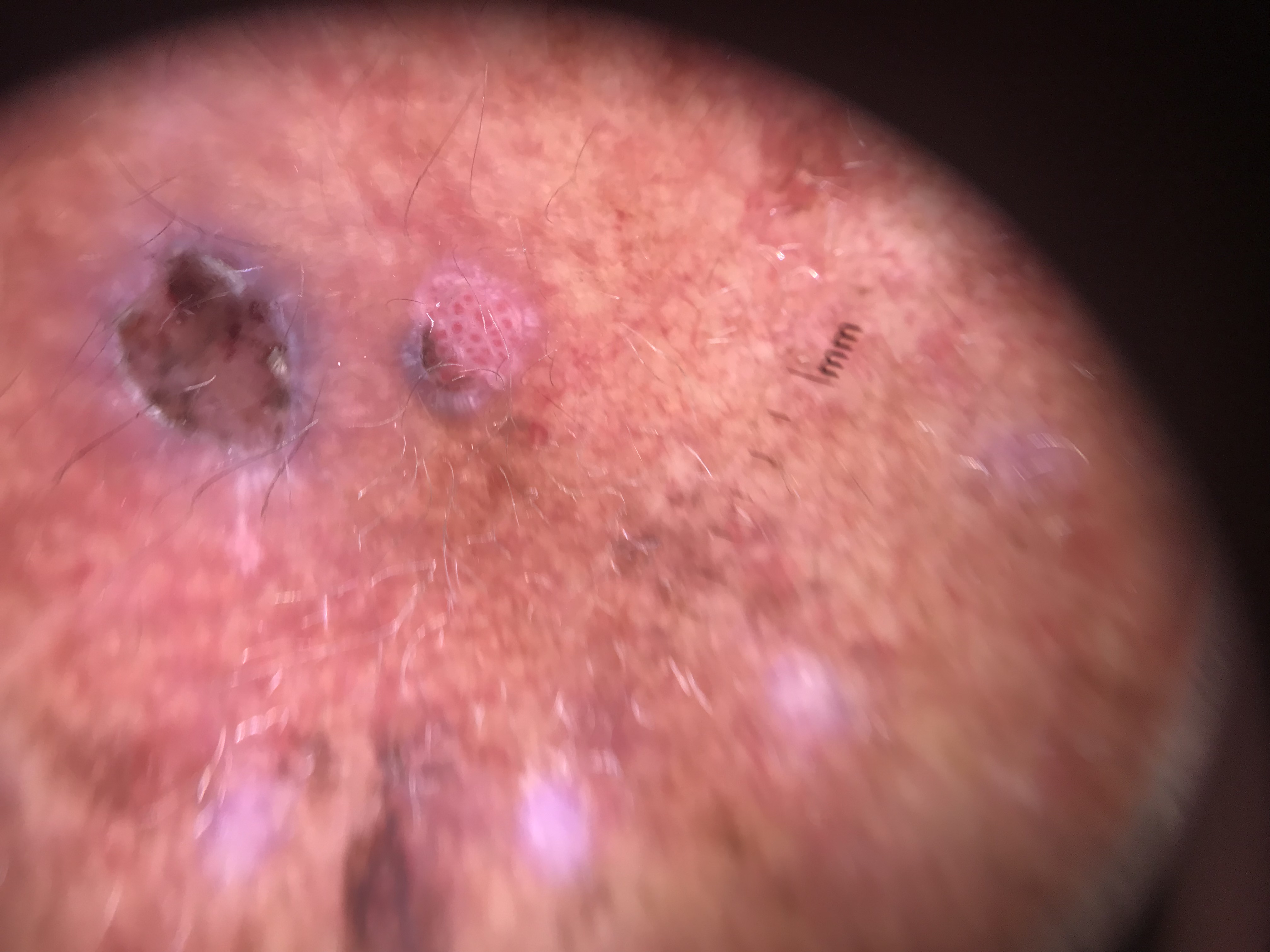Histopathology confirmed a basal cell carcinoma.